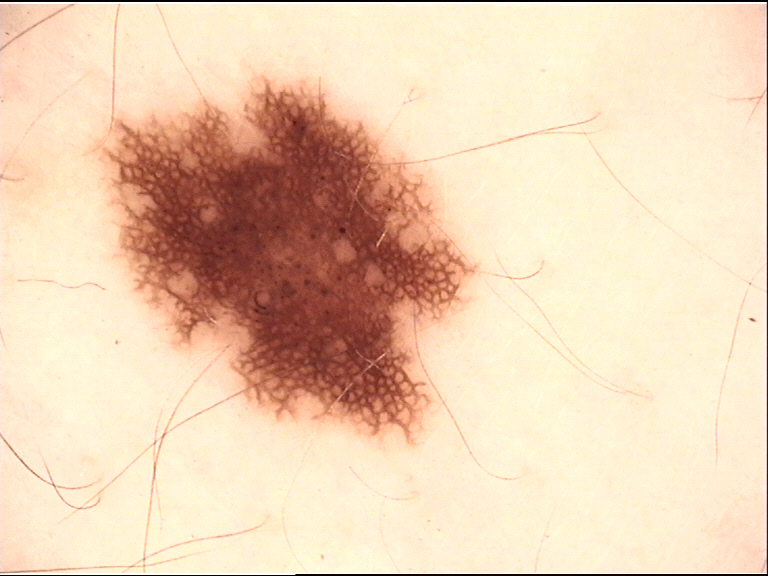A dermoscopy image of a single skin lesion.
The morphology is that of a banal lesion.
The diagnostic label was a junctional nevus.